A dermoscopic close-up of a skin lesion. A male patient approximately 70 years of age. The patient was assessed as FST II.
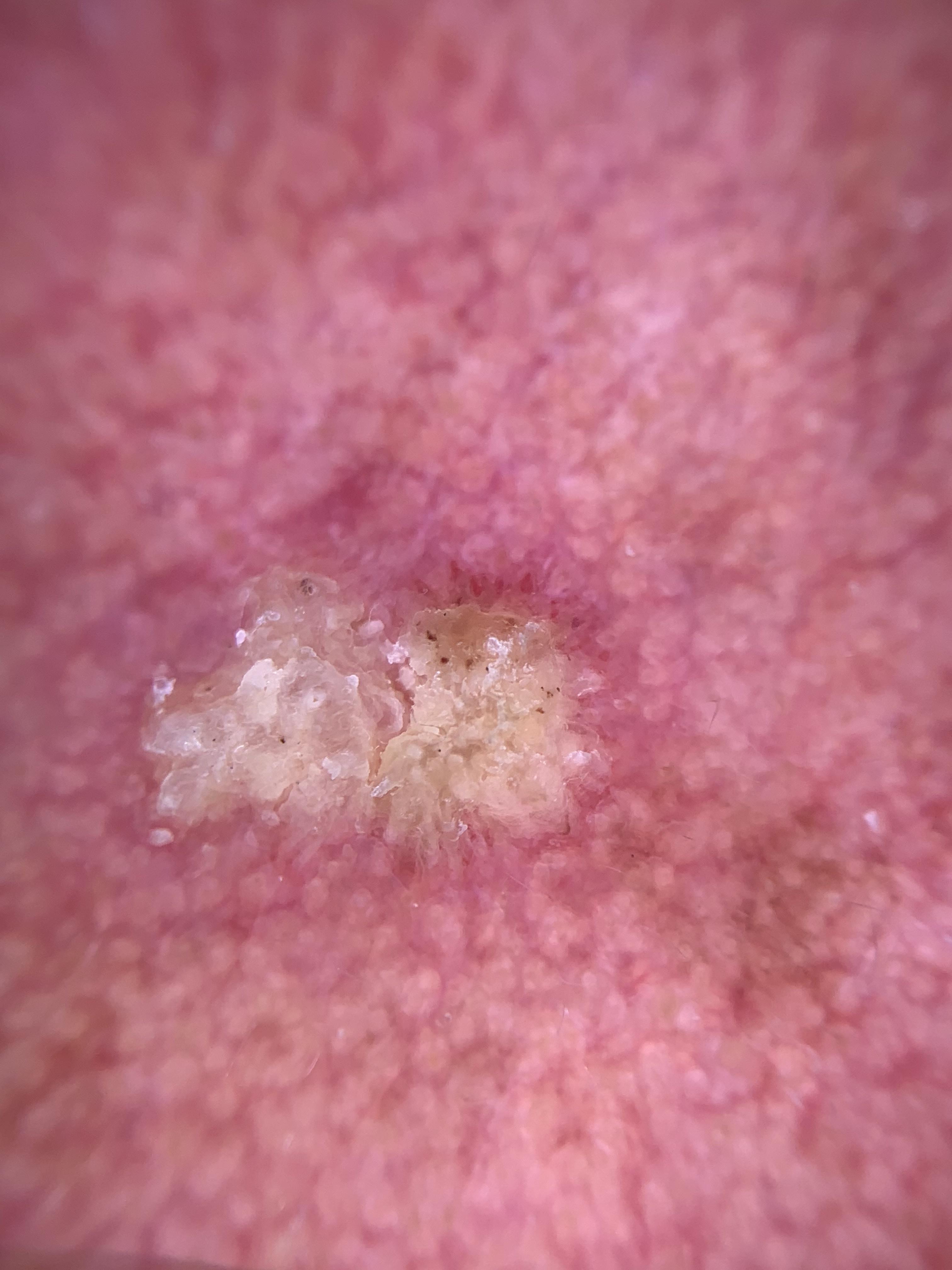The lesion is located on the head or neck.
Confirmed on histopathology as a malignant, epidermal lesion — a squamous cell carcinoma.